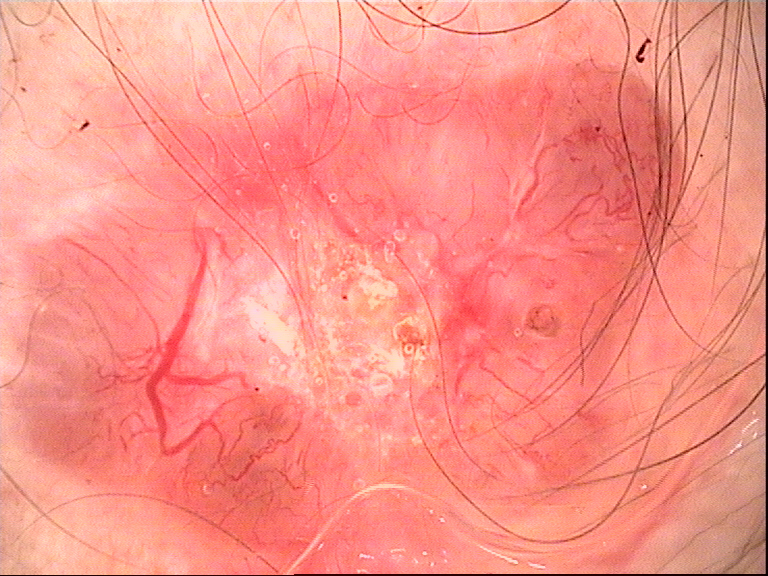pathology: basal cell carcinoma (biopsy-proven).